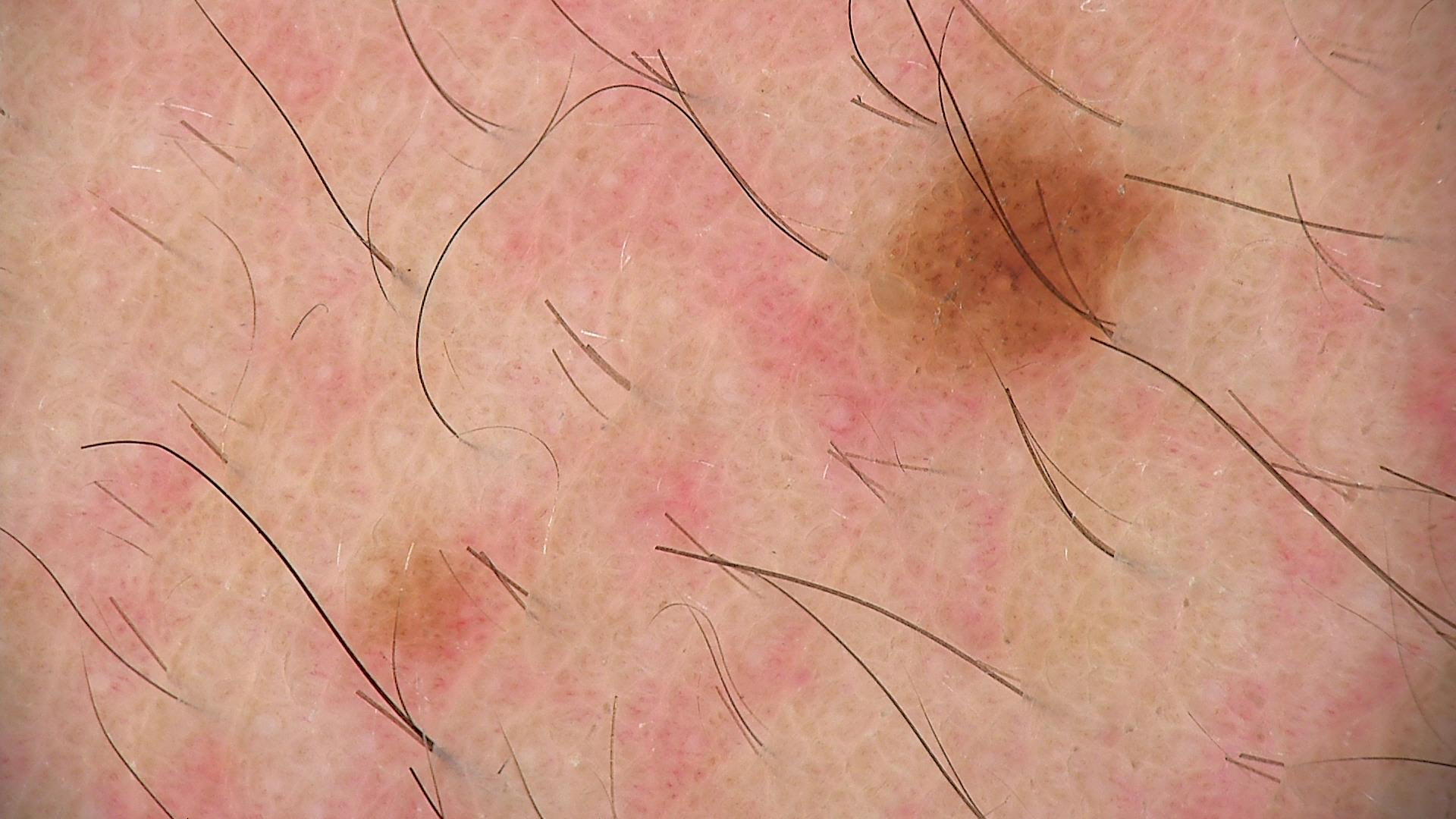Dermoscopy of a skin lesion. The diagnostic label was a dysplastic junctional nevus.